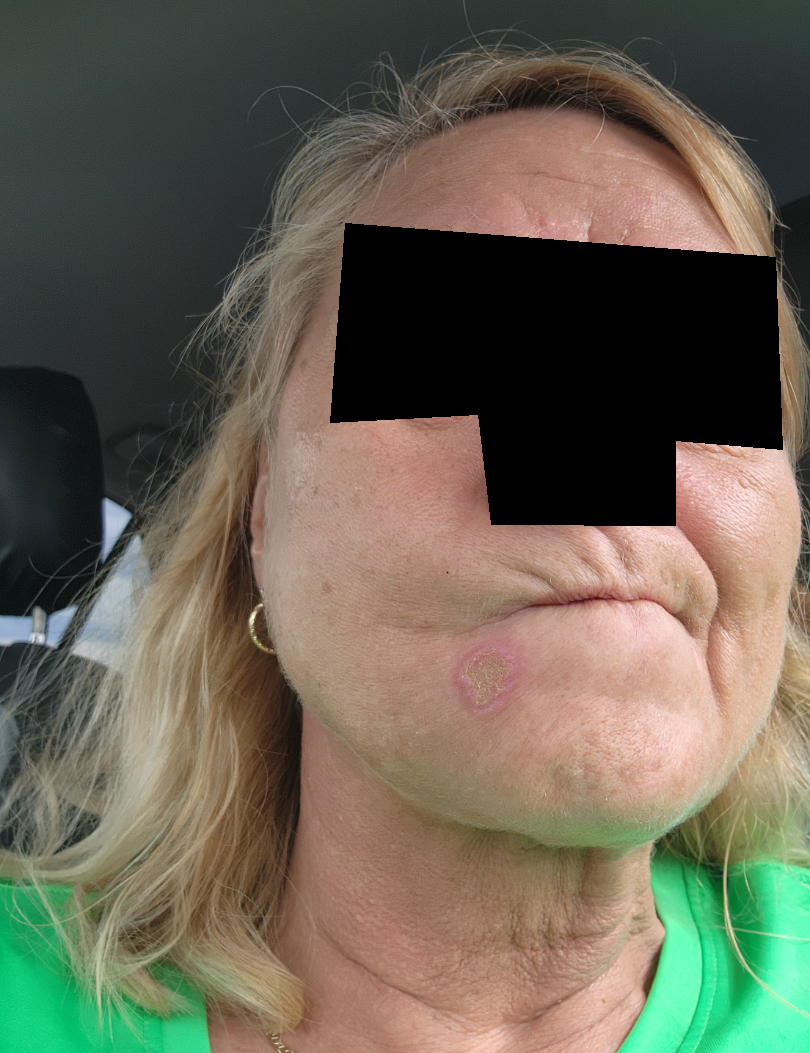dermatologist impression: the differential is split between Eruptive odontogenic cyst, Basal Cell Carcinoma and SCC/SCCIS.